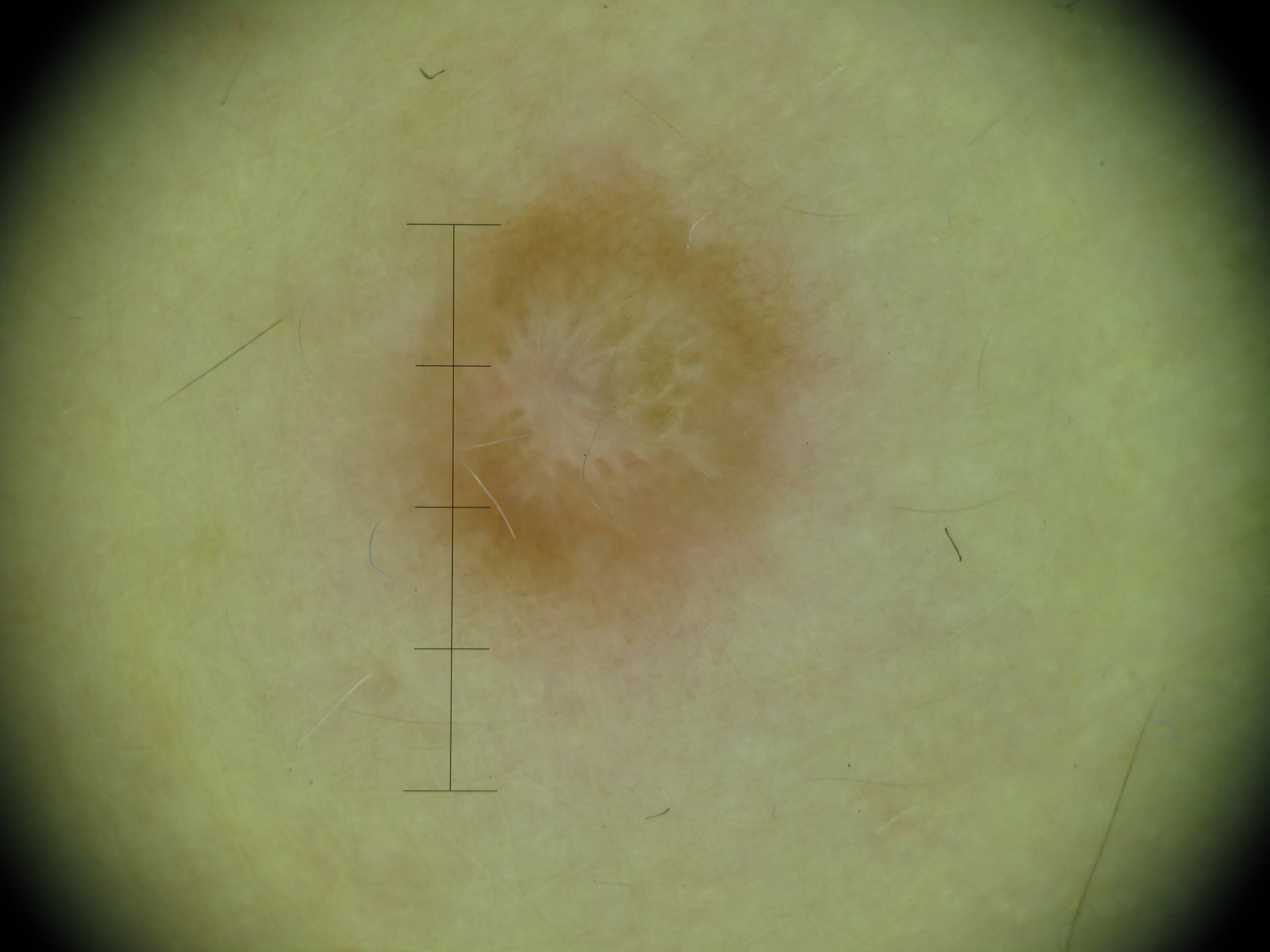Summary:
A dermatoscopic image of a skin lesion.
Impression:
Labeled as a benign lesion — a dermatofibroma.